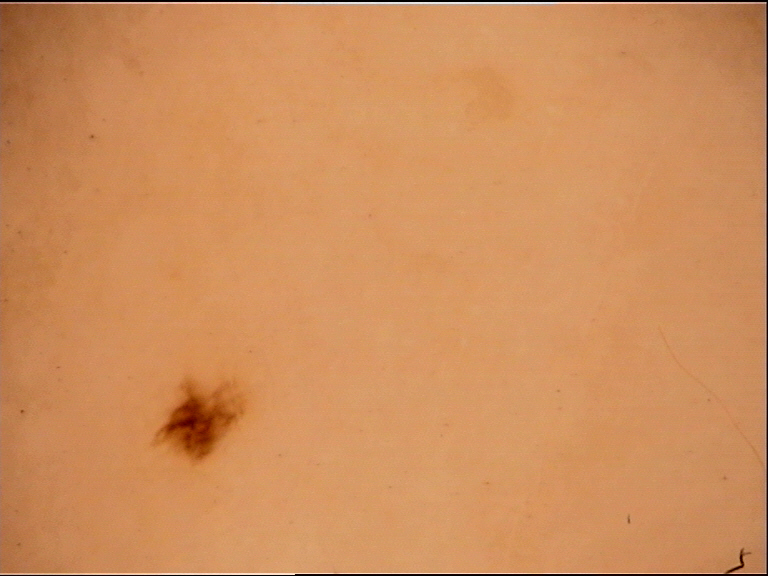Dermoscopy of a skin lesion. The diagnosis was an acral dysplastic junctional nevus.